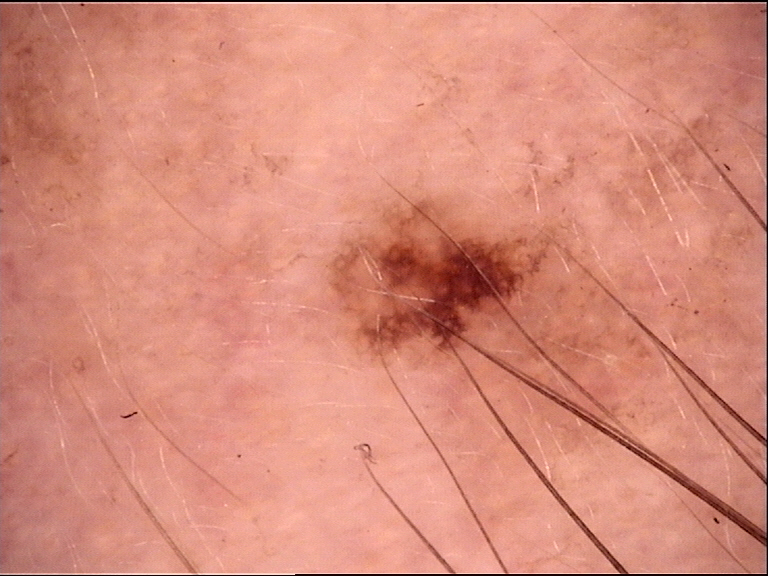A dermatoscopic image of a skin lesion.
The diagnosis was a dysplastic junctional nevus.